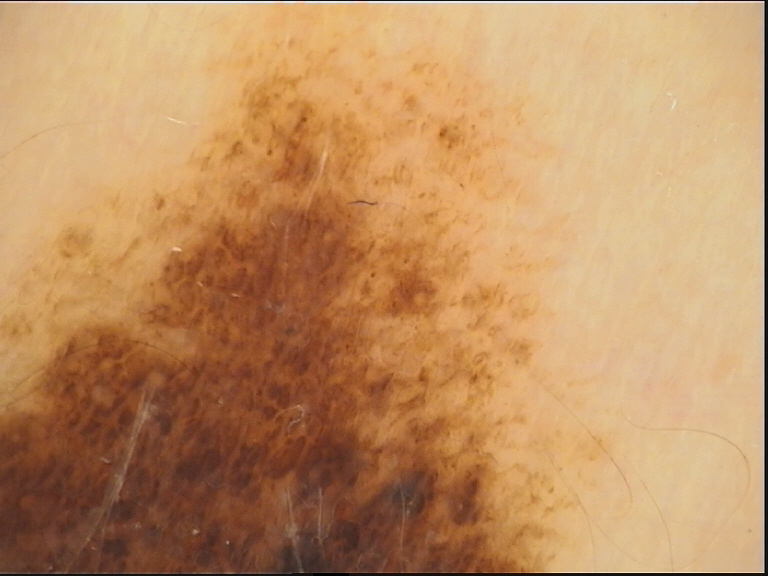Q: What was the diagnostic impression?
A: congenital compound nevus (expert consensus)